Female patient, age 30–39. The arm is involved. This image was taken at a distance.
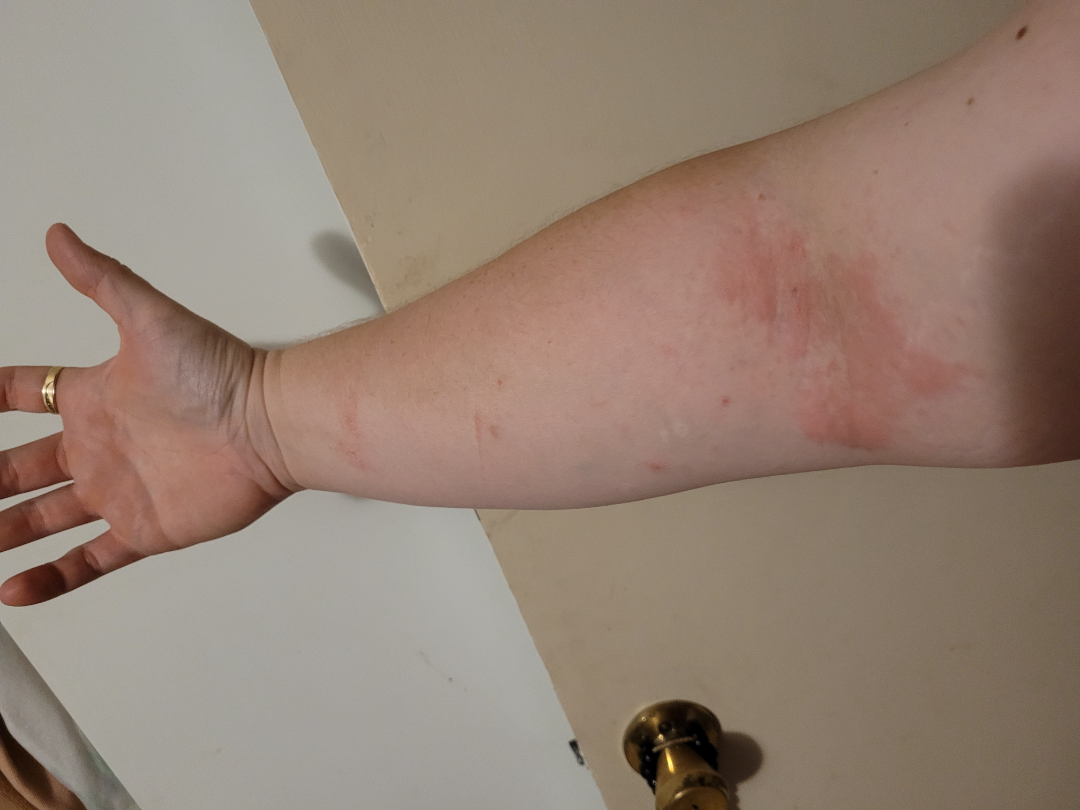Texture is reported as raised or bumpy.
Self-categorized by the patient as a rash.
The condition has been present for less than one week.
Symptoms reported: enlargement, bothersome appearance and itching.
On dermatologist assessment of the image, Eczema (100%).